The lesion involves the leg, close-up view: 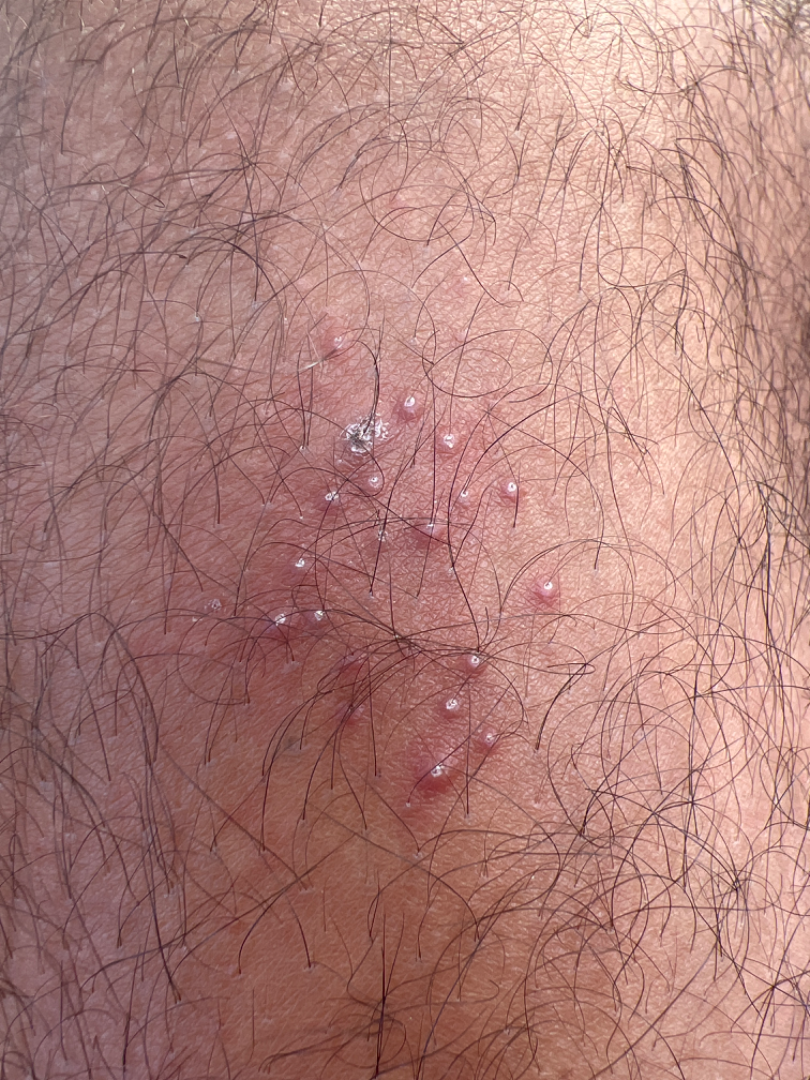On remote review of the image: Herpes Simplex (primary); Folliculitis (considered).